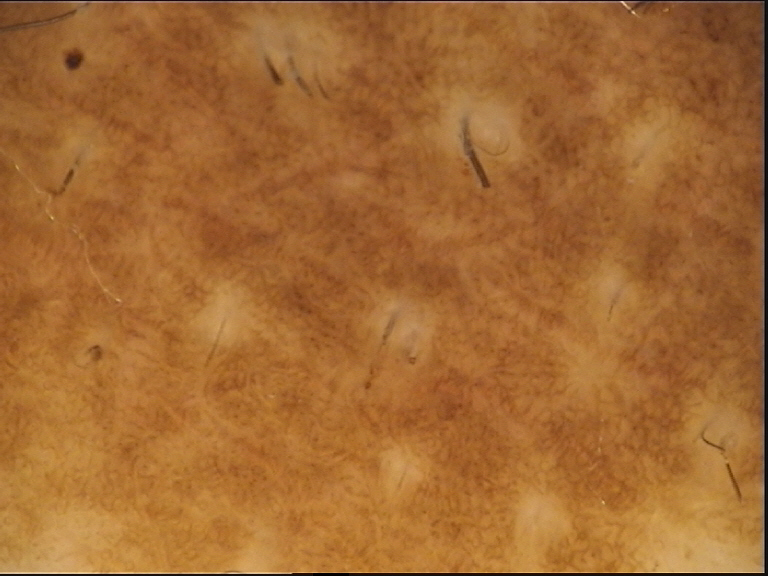imaging: dermoscopy
label: congenital compound nevus (expert consensus)